Present for one to four weeks · texture is reported as raised or bumpy and rough or flaky · female patient, age 40–49 · the leg is involved · the patient described the issue as a rash · FST IV; lay graders estimated Monk skin tone scale 3 or 6 · the photo was captured at an angle: 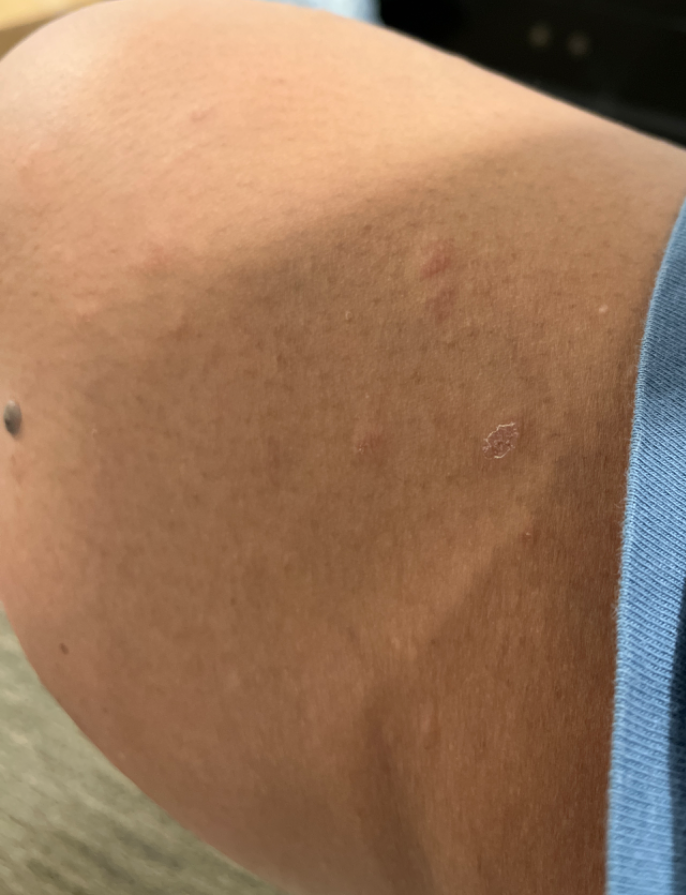Case summary:
- assessment: the leading consideration is Eczema